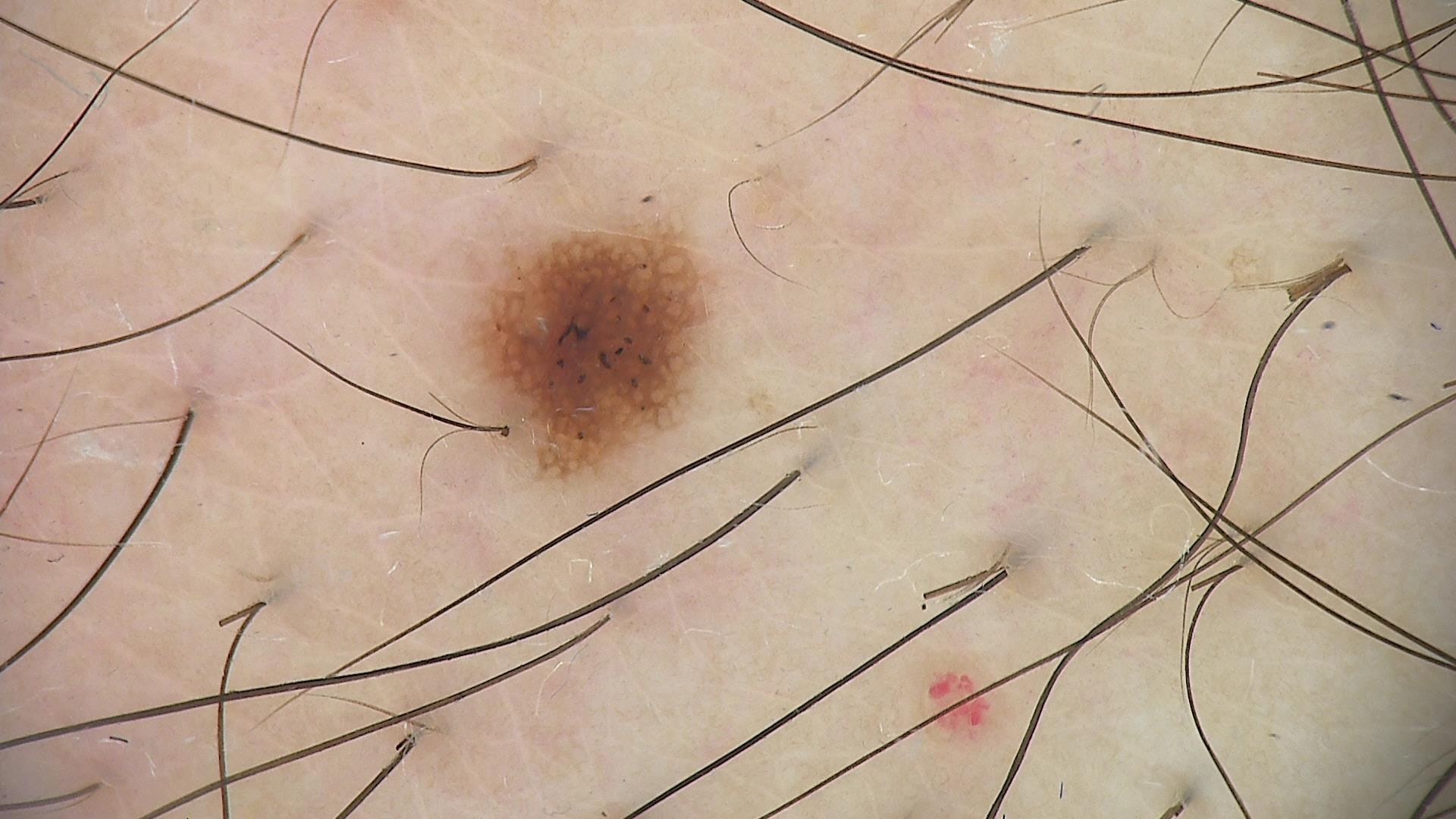image type — dermoscopy
class — dysplastic junctional nevus (expert consensus)